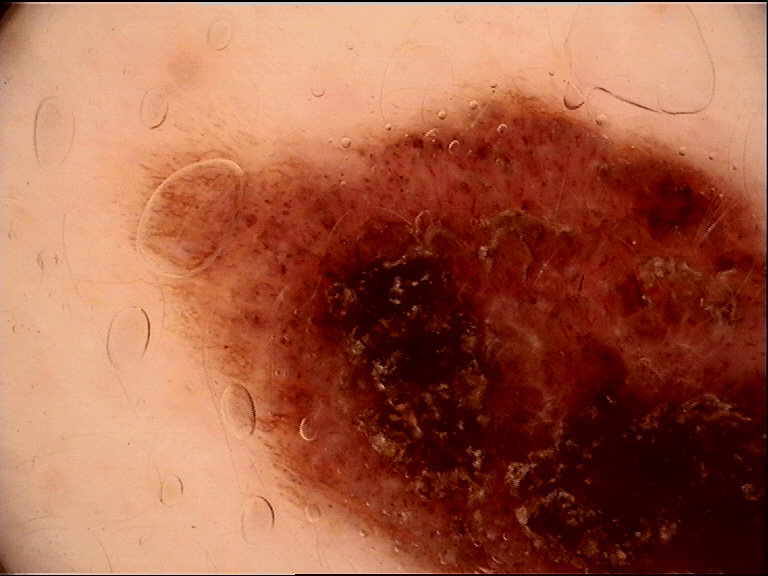Labeled as a congenital compound nevus.